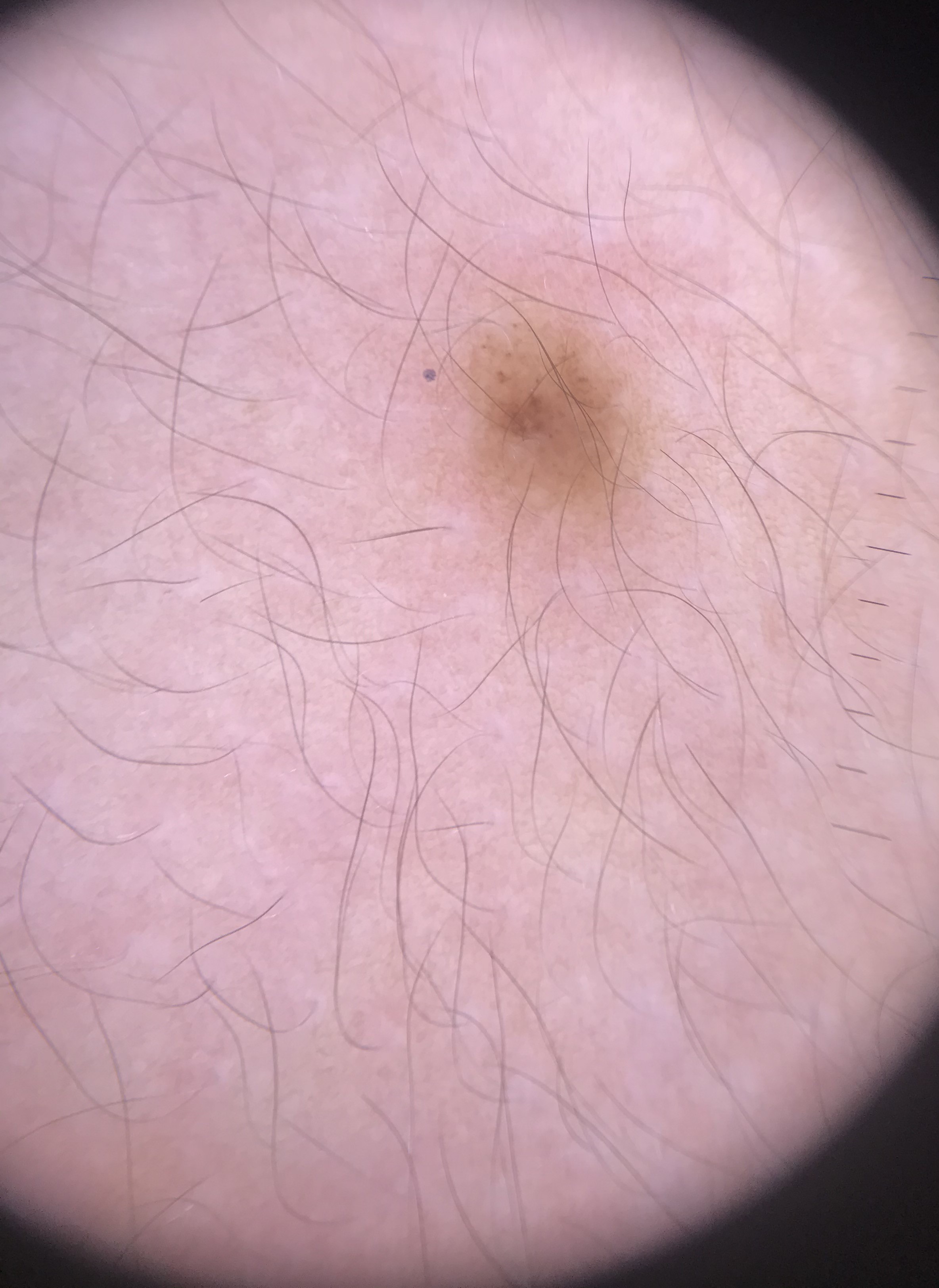Q: What kind of image is this?
A: dermatoscopy
Q: How is the lesion classified?
A: banal
Q: What was the diagnostic impression?
A: junctional nevus (expert consensus)